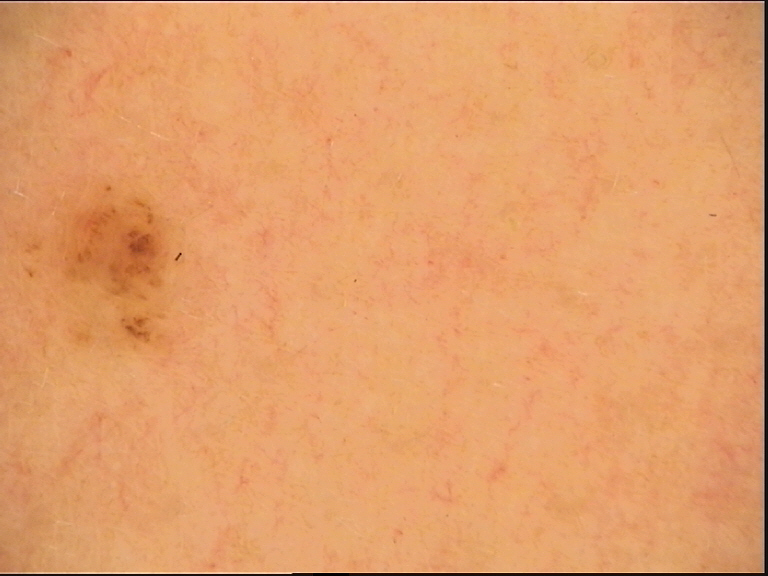Summary:
Dermoscopy of a skin lesion.
Conclusion:
Diagnosed as a banal lesion — a compound nevus.